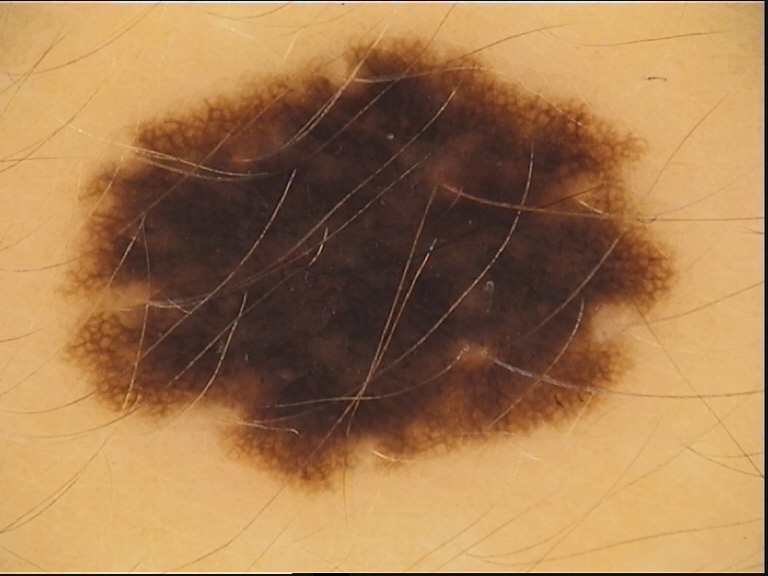Case:
* imaging: dermatoscopy
* diagnostic label: dysplastic compound nevus (expert consensus)